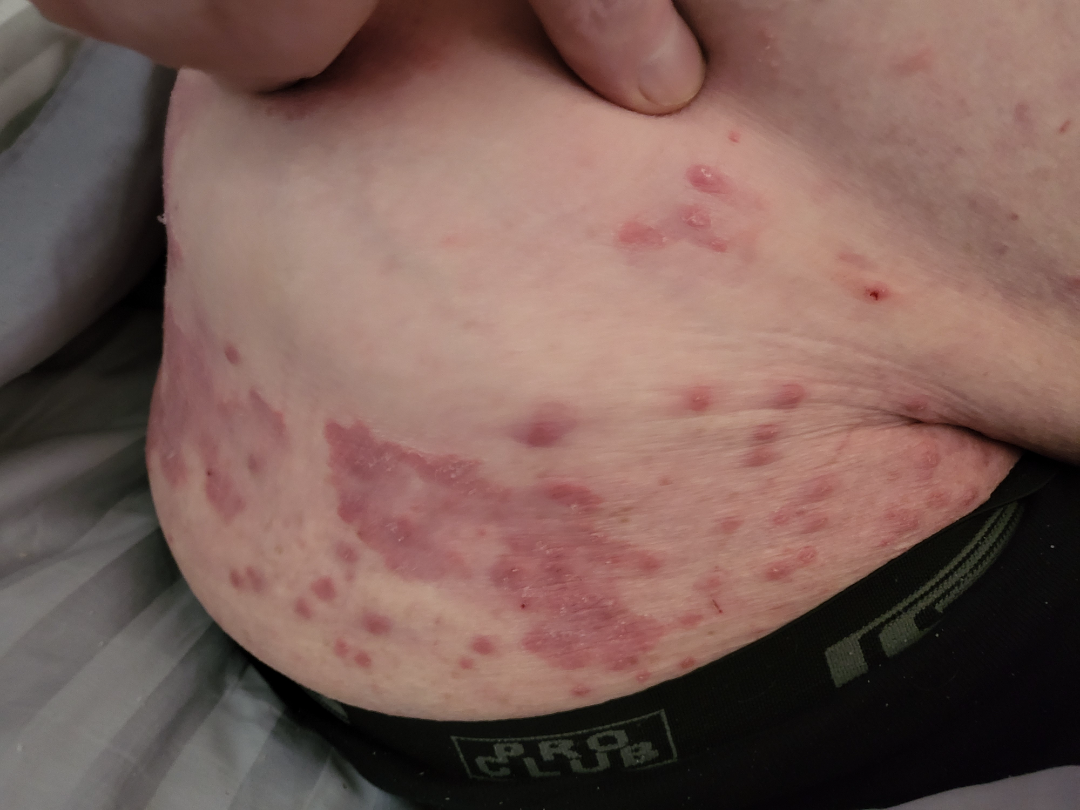The case was indeterminate on photographic review.
Skin tone: Fitzpatrick III; non-clinician graders estimated a MST of 2.
Close-up view.